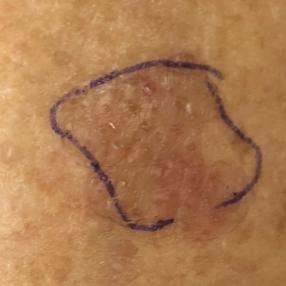Clinically diagnosed as an actinic keratosis.